A skin lesion imaged with a dermatoscope.
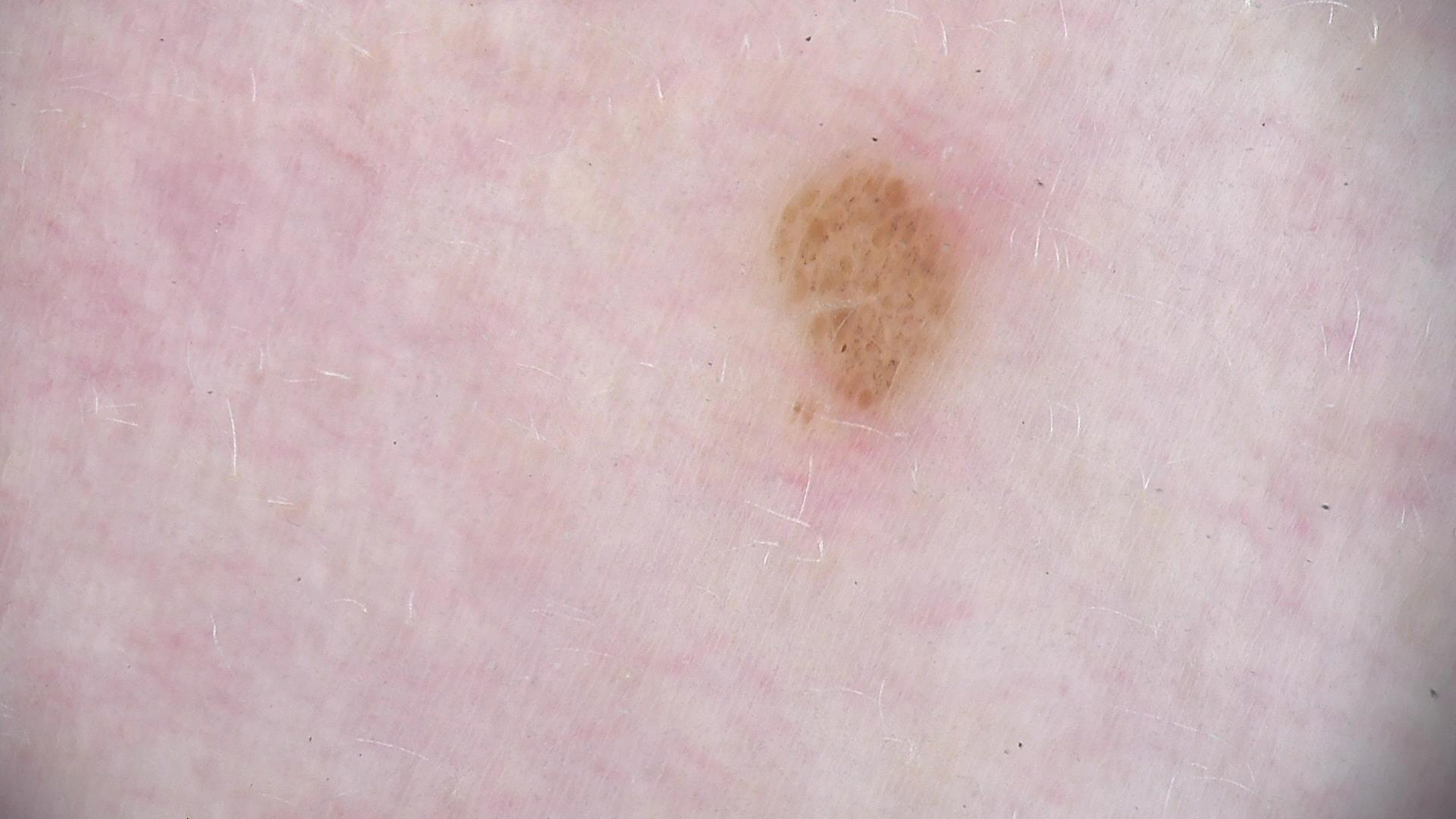  diagnosis:
    name: compound nevus
    code: cb
    malignancy: benign
    super_class: melanocytic
    confirmation: expert consensus